FST II; a female patient 64 years old; by history, prior skin cancer (patient or family), pesticide exposure, no alcohol use, and no tobacco use; a clinical close-up photograph of a skin lesion:
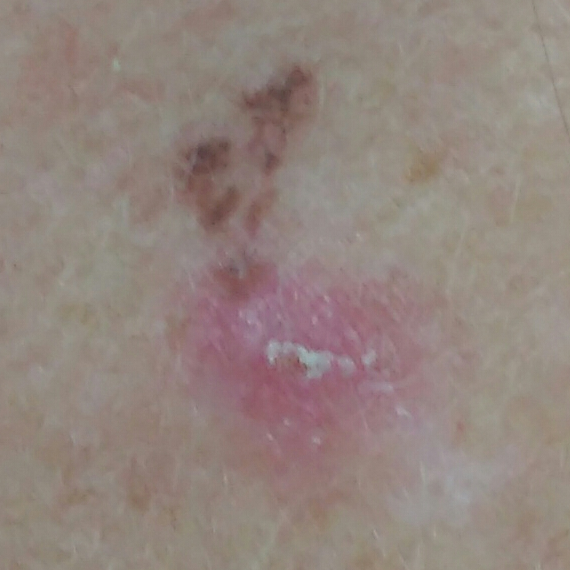The lesion measures 16 × 15 mm.
The patient describes that the lesion has grown.
Histopathological examination showed a basal cell carcinoma.